The chart notes no prior malignancy (patient or family) · a female subject age 84 · a clinical photo of a skin lesion taken with a smartphone · recorded as Fitzpatrick skin type II:
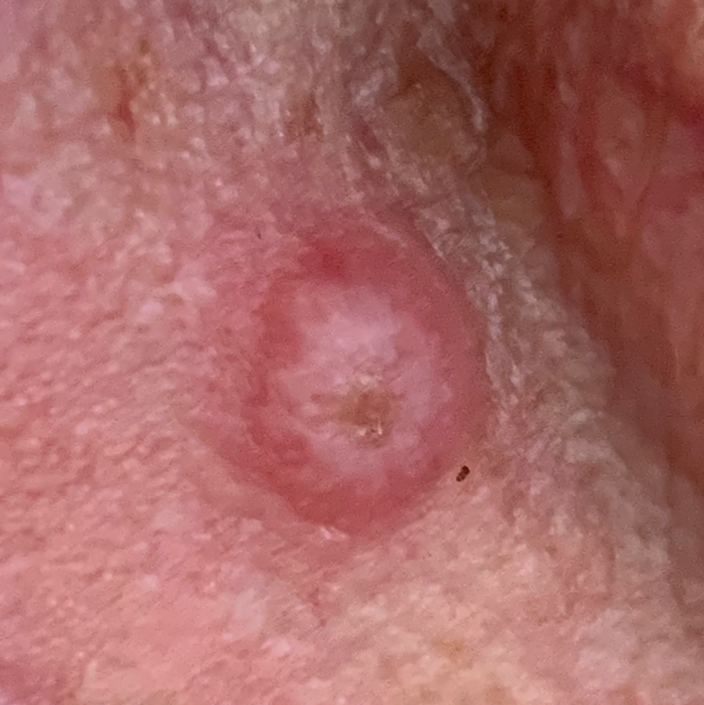body site = the nose; lesion size = approx. 7 × 6 mm; patient-reported symptoms = elevation / no pain, no bleeding; pathology = squamous cell carcinoma (biopsy-proven).